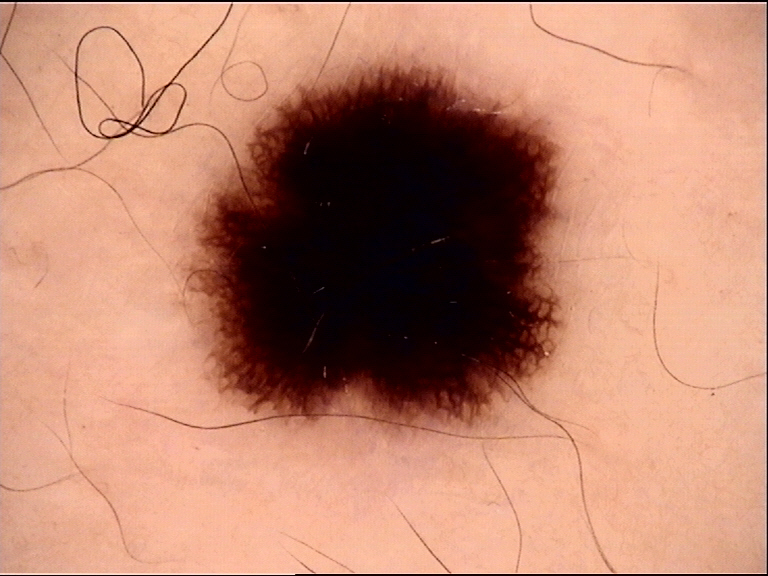Conclusion: The diagnosis was a Spitz/Reed nevus.